The head or neck and leg are involved, the photo was captured at a distance.
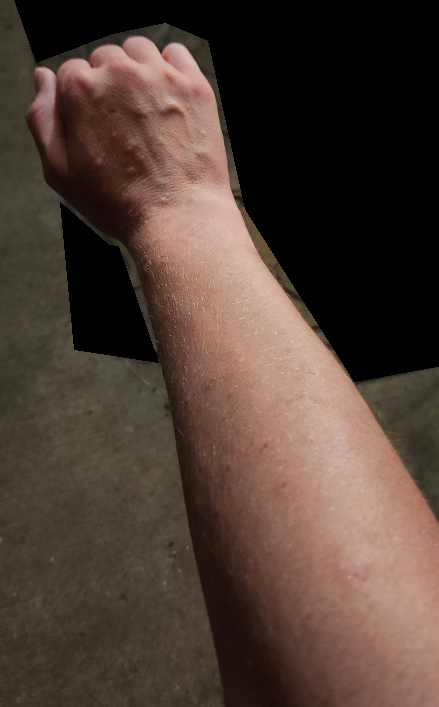assessment = ungradable on photographic review; present for = one to four weeks; lesion texture = raised or bumpy and fluid-filled; self-categorized as = a rash.